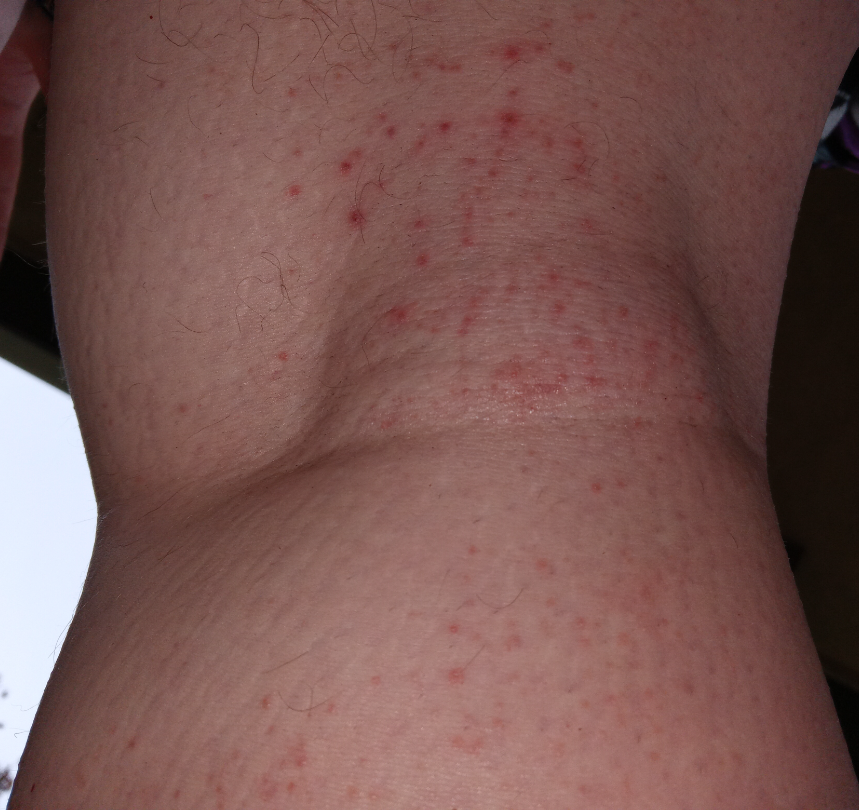duration = less than one week
skin tone = non-clinician graders estimated Monk Skin Tone 2
patient = female, age 18–29
body site = arm
constitutional symptoms = none reported
symptoms = pain, itching and burning
image framing = close-up
diagnostic considerations = favoring Eczema; lower on the differential is Folliculitis; less probable is Leukocytoclastic Vasculitis; less likely is Pruritic dermatitis